The patient considered this a rash · the patient reports the lesion is raised or bumpy · reported lesion symptoms include itching · this is a close-up image · the patient reports the condition has been present for less than one week · the affected area is the arm, back of the torso, front of the torso, leg and back of the hand.
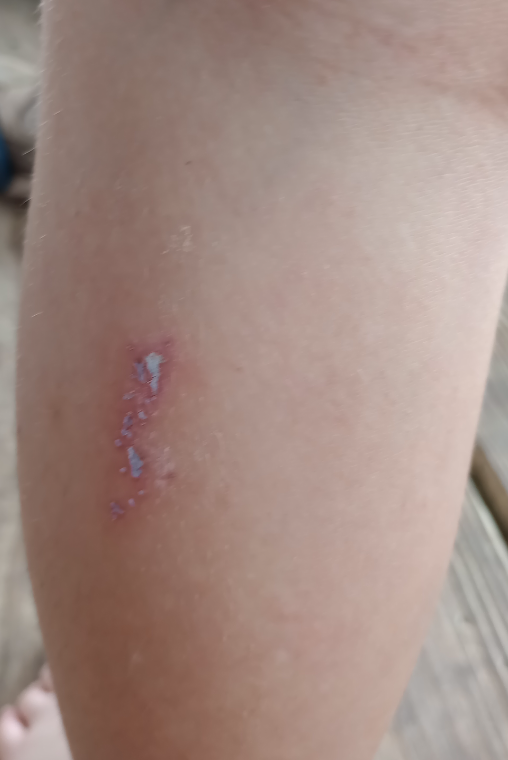  assessment: indeterminate from the photograph